The affected area is the head or neck, leg and back of the torso; close-up view.
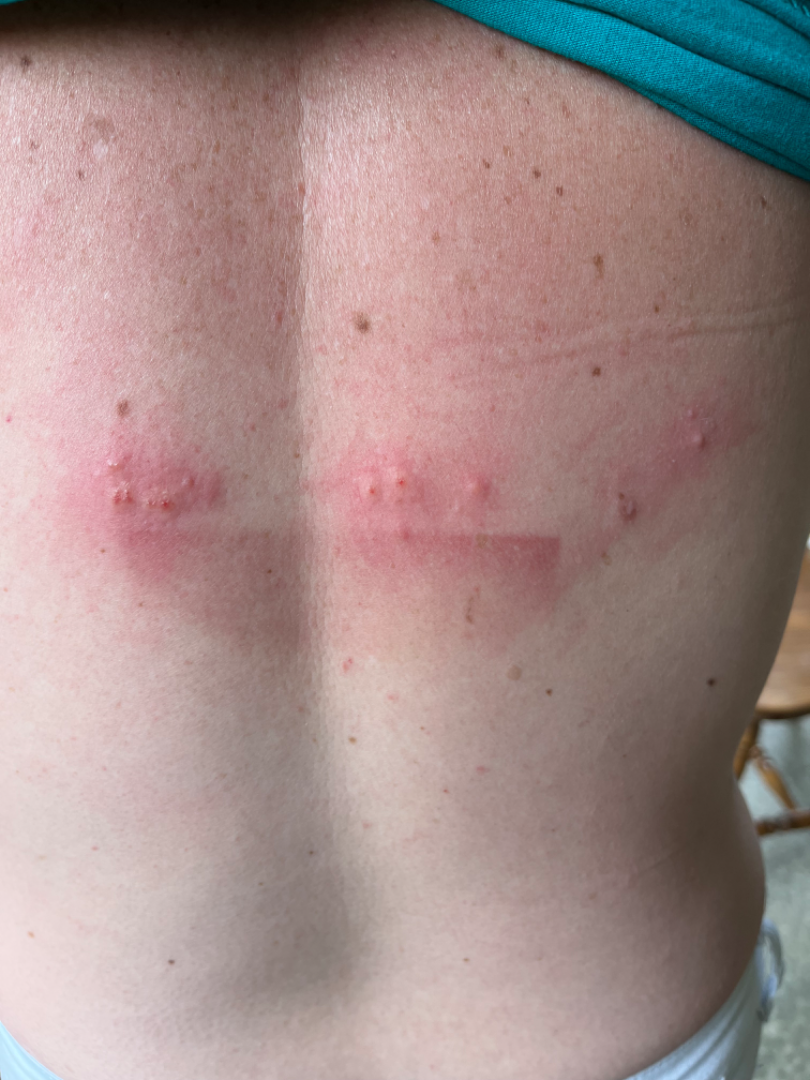{"assessment": "ungradable on photographic review"}